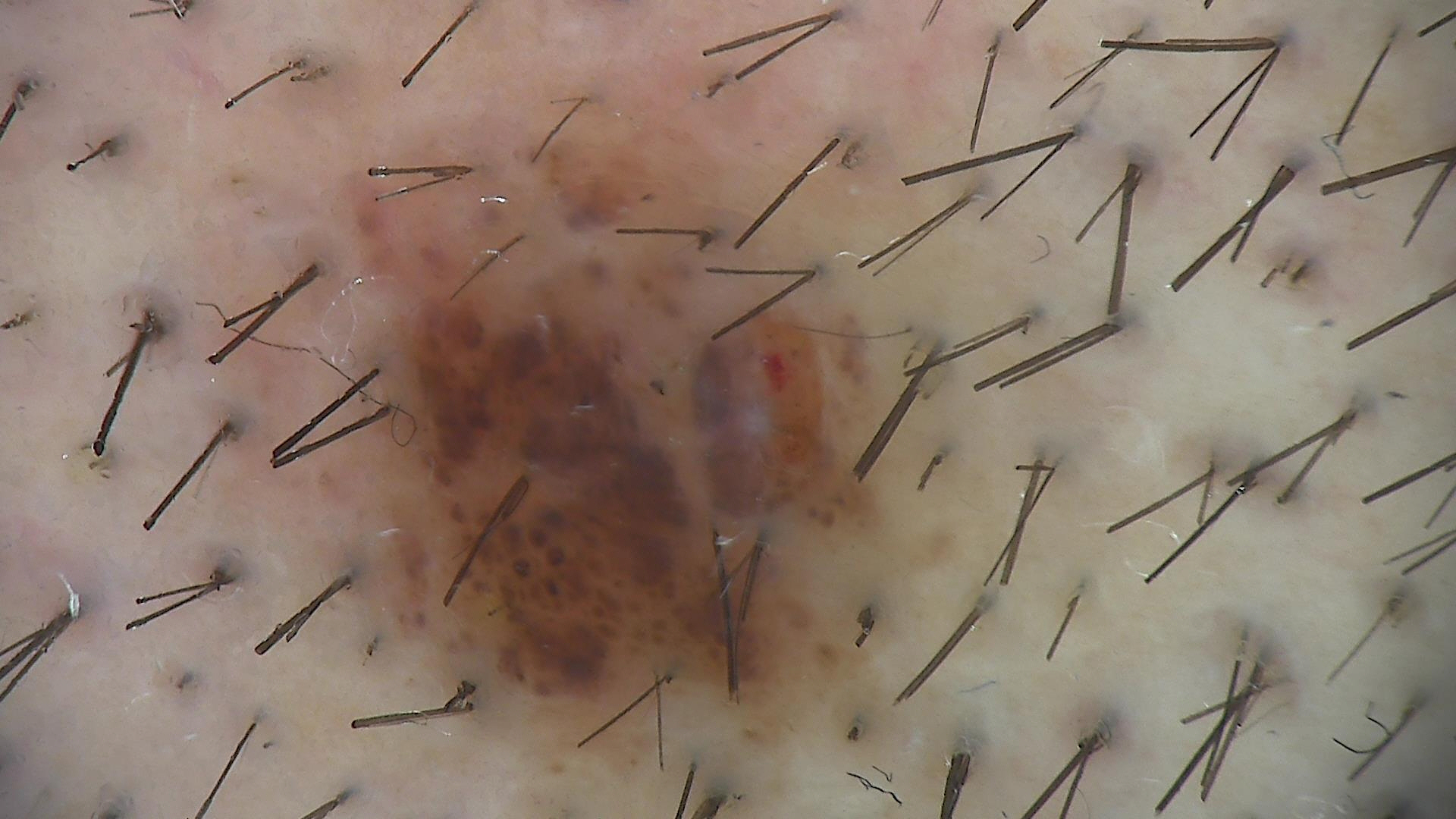diagnosis = compound nevus (expert consensus).